The photo was captured at an angle.
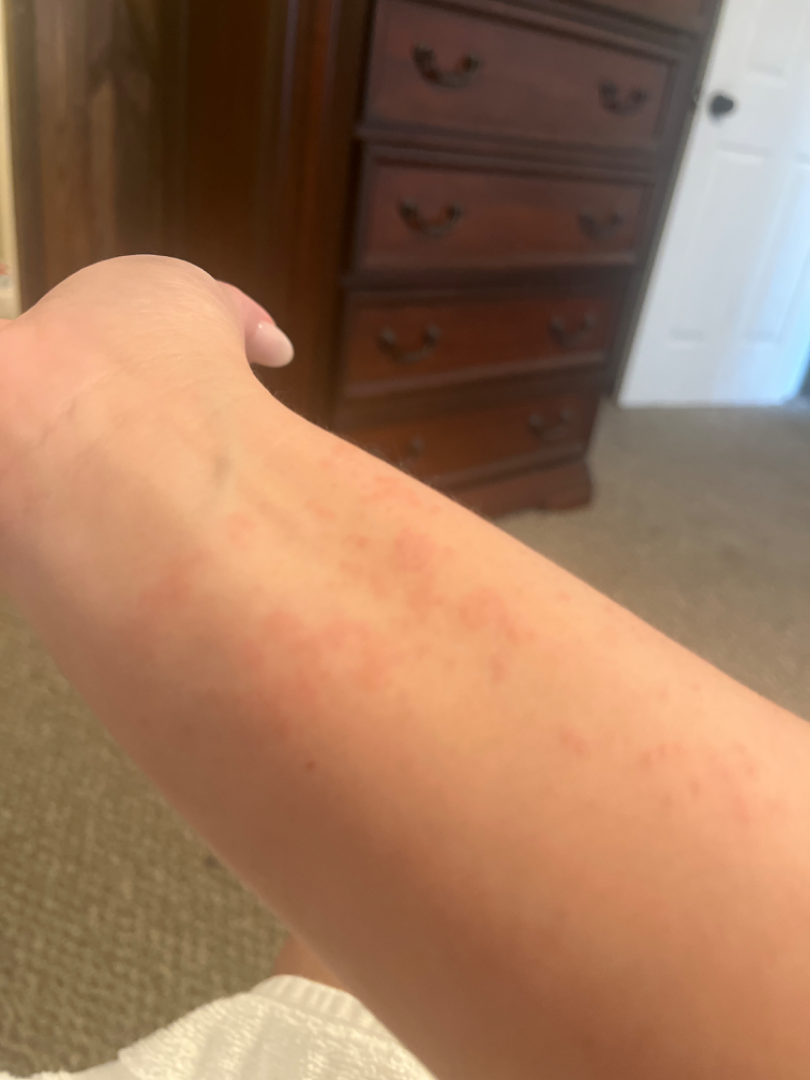{"assessment": "not assessable"}